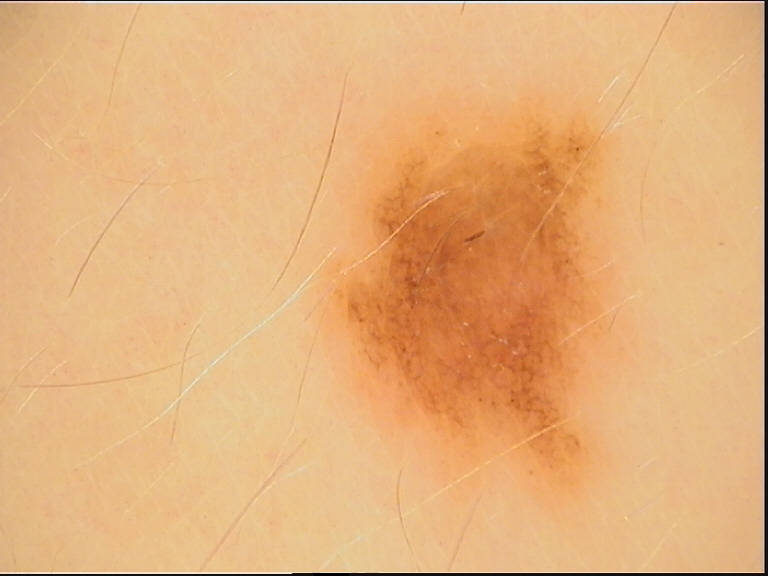{
  "image": "dermatoscopy",
  "diagnosis": {
    "name": "dysplastic junctional nevus",
    "code": "jd",
    "malignancy": "benign",
    "super_class": "melanocytic",
    "confirmation": "expert consensus"
  }
}